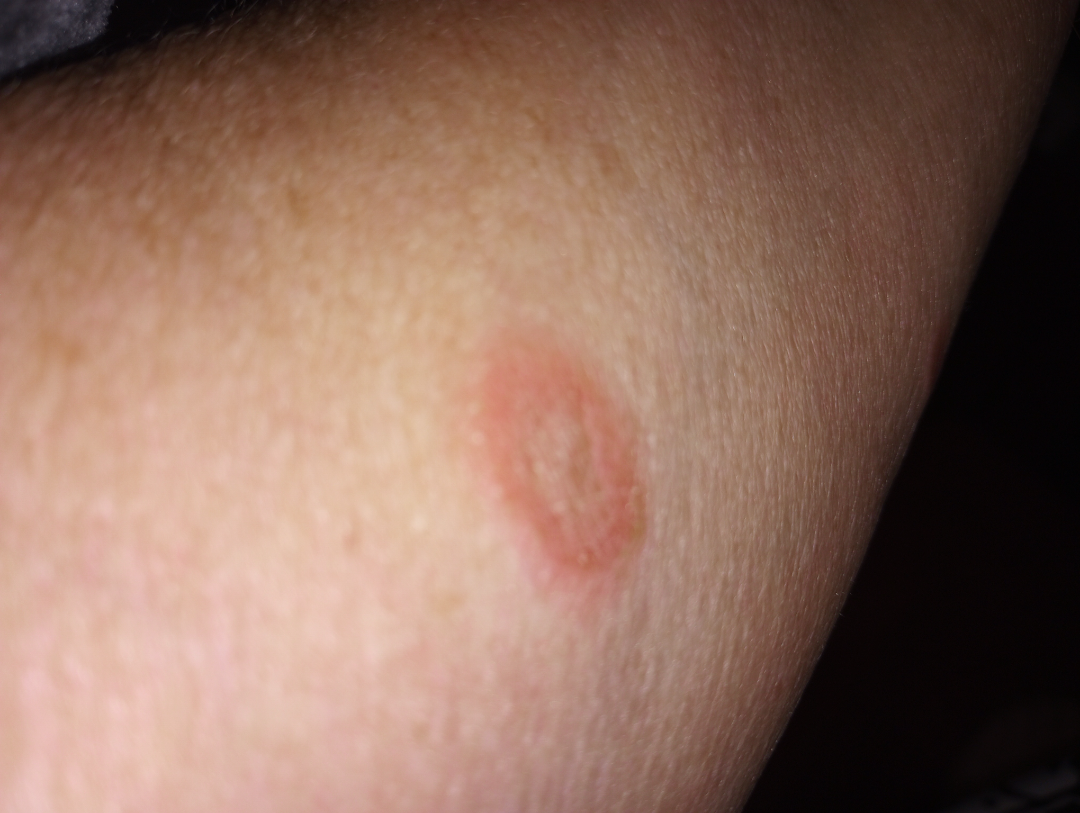The subject is a female aged 60–69. Reported lesion symptoms include bothersome appearance and enlargement. Reported duration is less than one week. The photograph is a close-up of the affected area. Self-categorized by the patient as a rash. The affected area is the arm. The differential, in no particular order, includes Impetigo, Insect Bite and Erythema migrans.